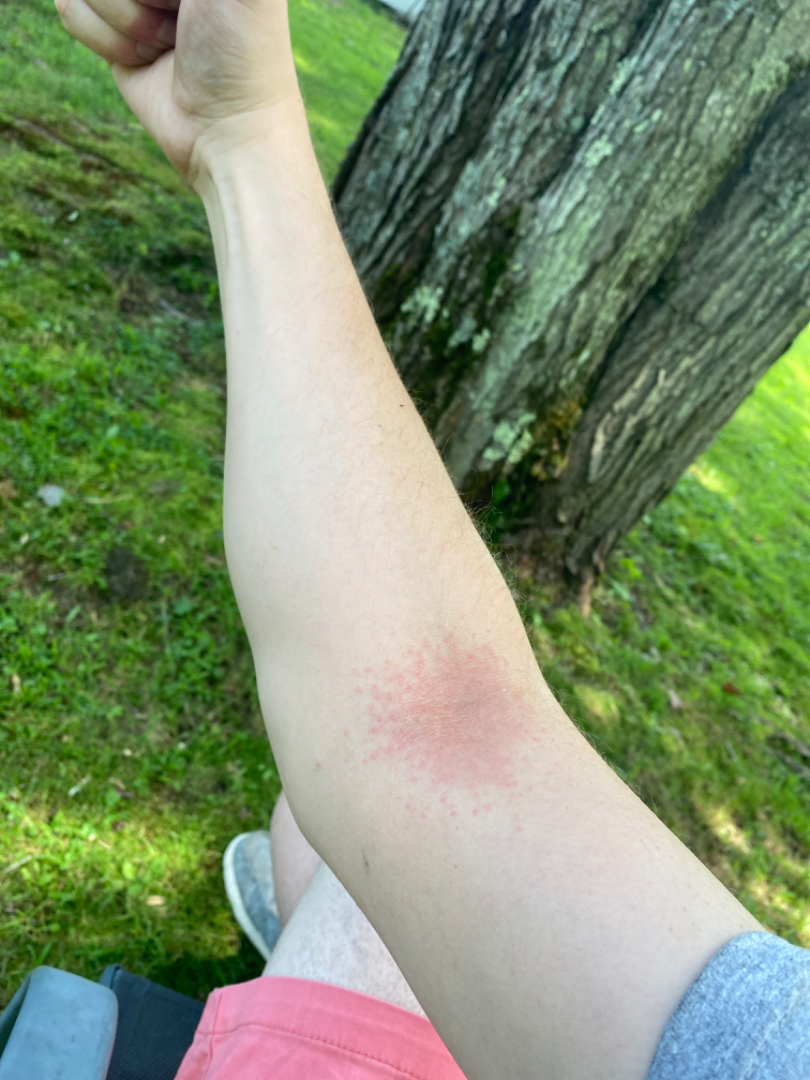photo taken: at a distance
affected area: arm
skin tone: Fitzpatrick II
surface texture: raised or bumpy and rough or flaky
onset: one to three months
patient's own categorization: a rash
patient-reported symptoms: itching
other reported symptoms: none reported
contributor: male, age 40–49
assessment: in keeping with Eczema